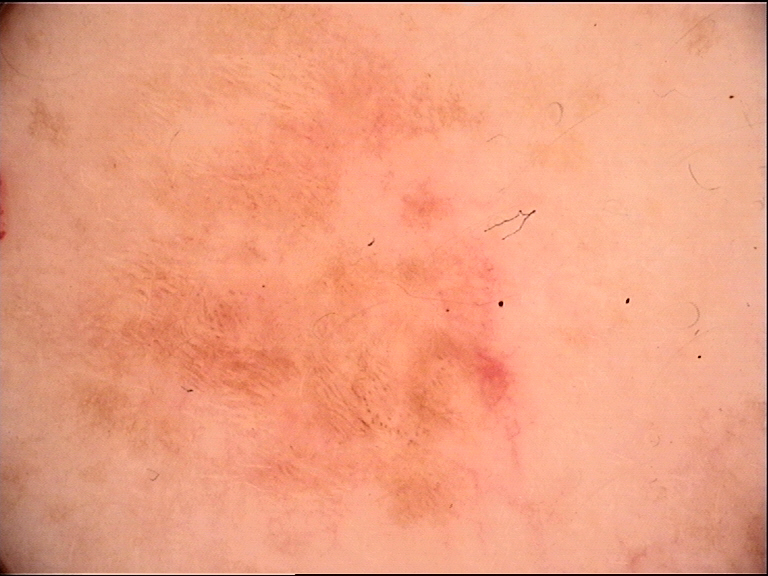The diagnostic label was a dysplastic junctional nevus.